Self-categorized by the patient as a rash · human graders estimated Monk skin tone scale 2 · close-up view · the contributor notes enlargement · the contributor is 50–59, female · no constitutional symptoms were reported · reported duration is one to three months · the lesion involves the leg:
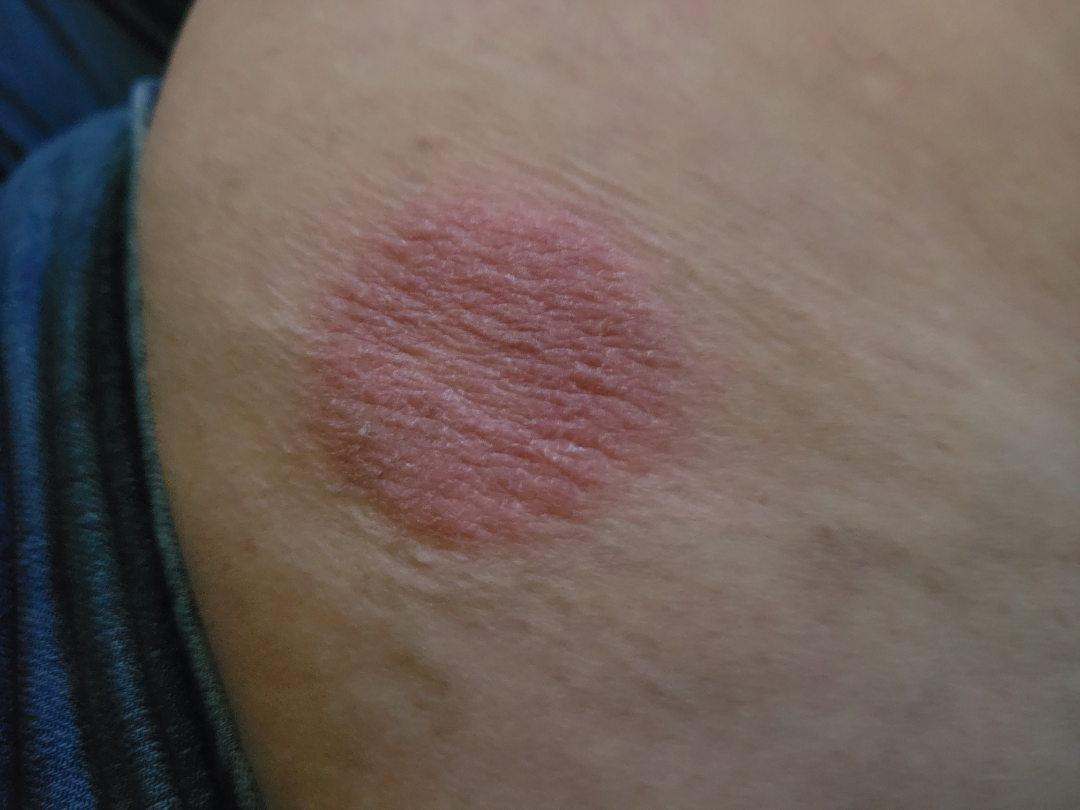<dermatology_case>
  <differential>
    <tied_lead>Psoriasis, Cutaneous T Cell Lymphoma</tied_lead>
  </differential>
</dermatology_case>